A skin lesion imaged with a dermatoscope — 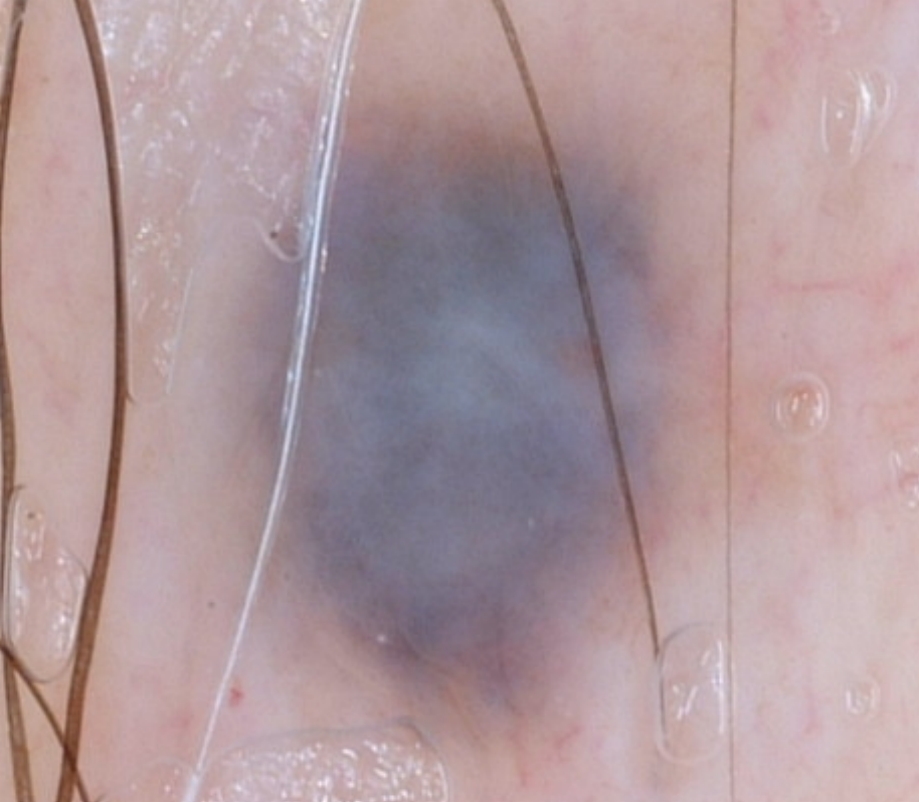A large lesion occupying much of the field. As (left, top, right, bottom), lesion location: bbox=[218, 98, 746, 763]. Dermoscopic review identifies no globules or streaks. The lesion was assessed as a benign lesion.